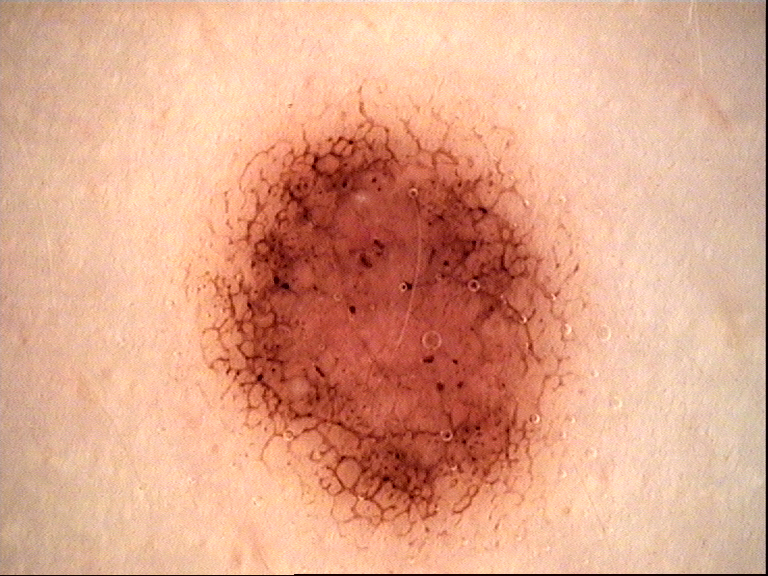| key | value |
|---|---|
| image type | dermoscopy |
| category | banal |
| assessment | compound nevus (expert consensus) |